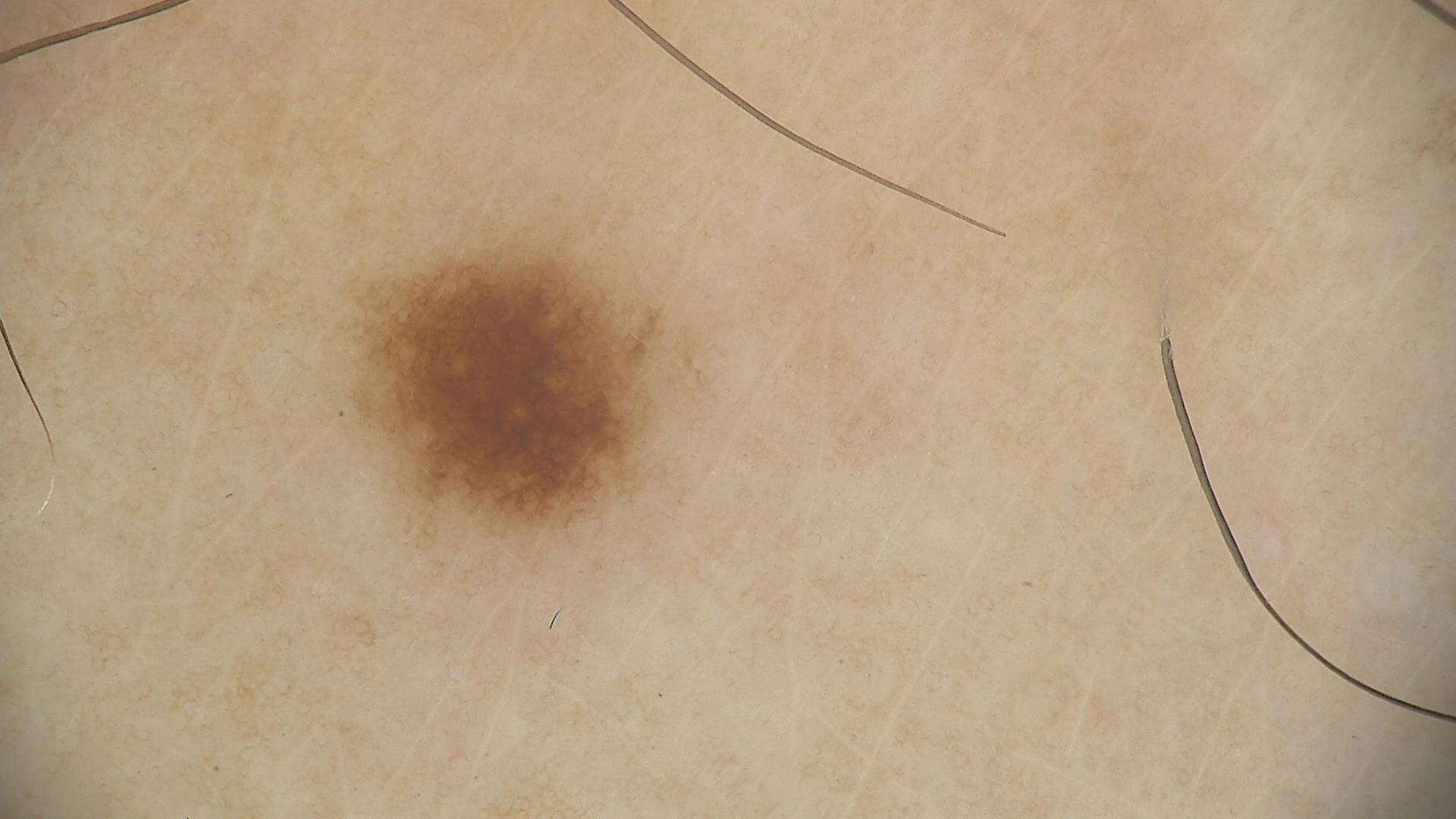Case:
– class — dysplastic junctional nevus (expert consensus)